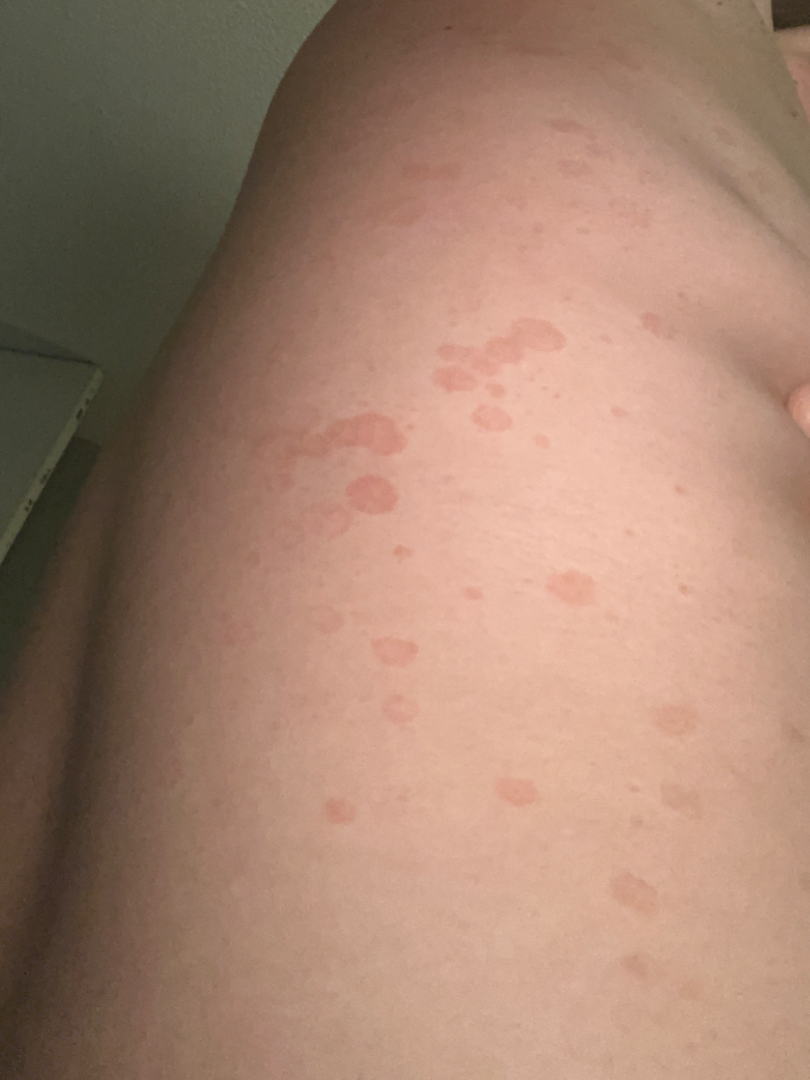On remote dermatologist review, Tinea Versicolor (possible); Seborrheic Dermatitis (possible).